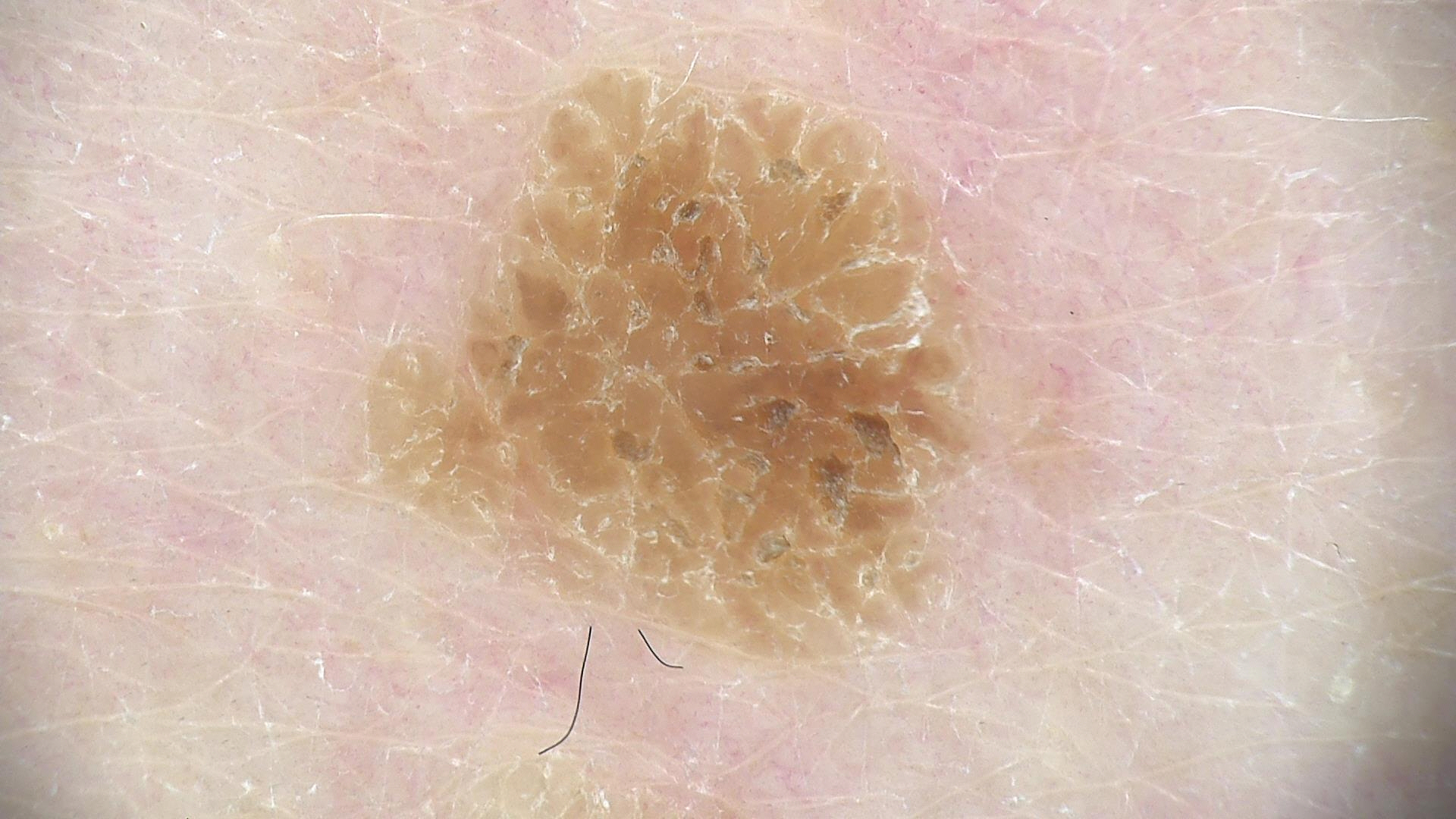Case:
* image — dermoscopy
* class — seborrheic keratosis (expert consensus)